The patient is FST II · an overview clinical photograph of a skin lesion · the chart documents a prior melanoma — 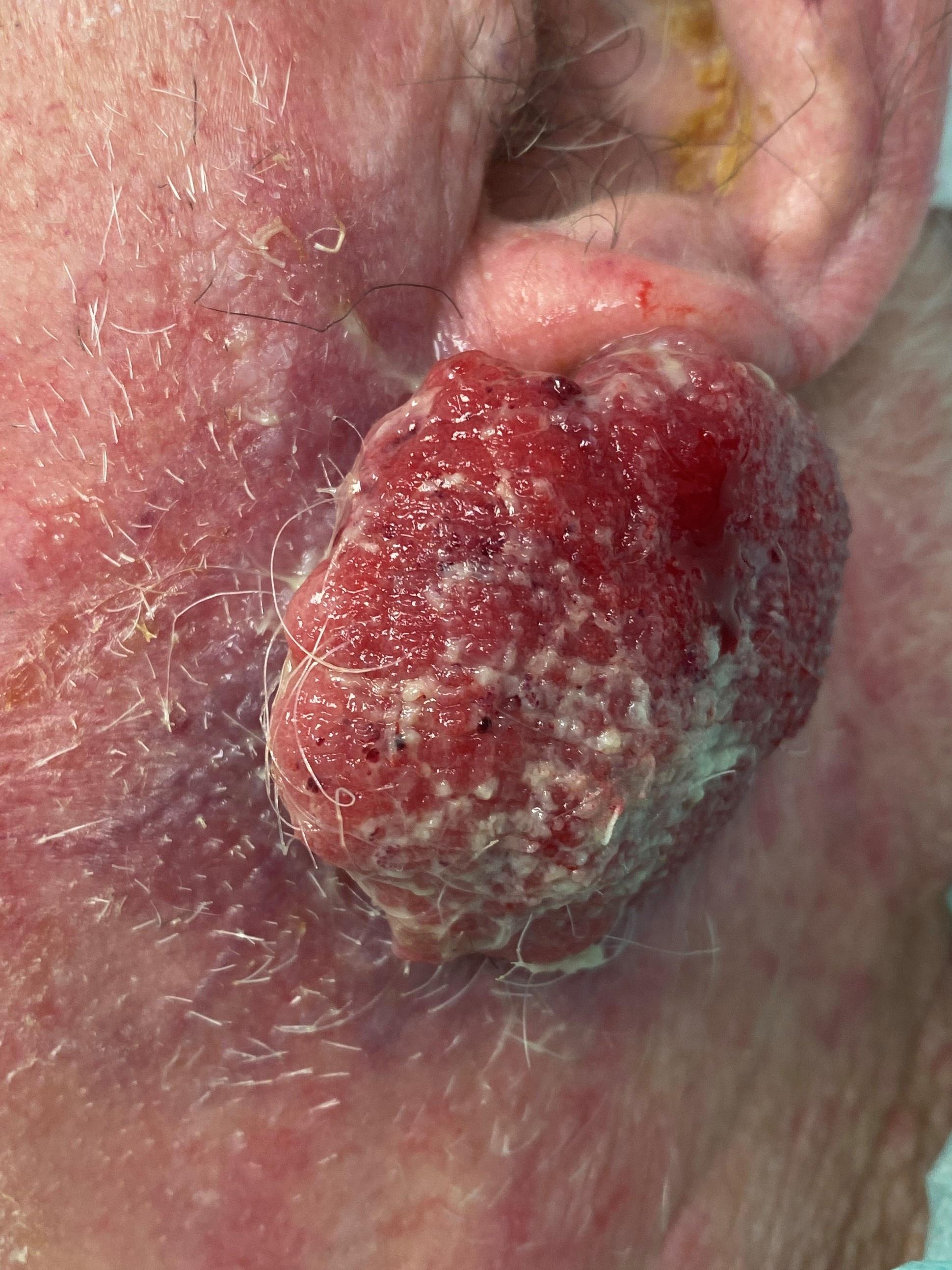The lesion is located on the head or neck. Biopsy-confirmed as a squamous cell carcinoma.